The affected area is the front of the torso. Self-categorized by the patient as a rash. Close-up view. The patient did not report lesion symptoms. The contributor reports the lesion is flat. Present for about one day. Female contributor, age 60–69.
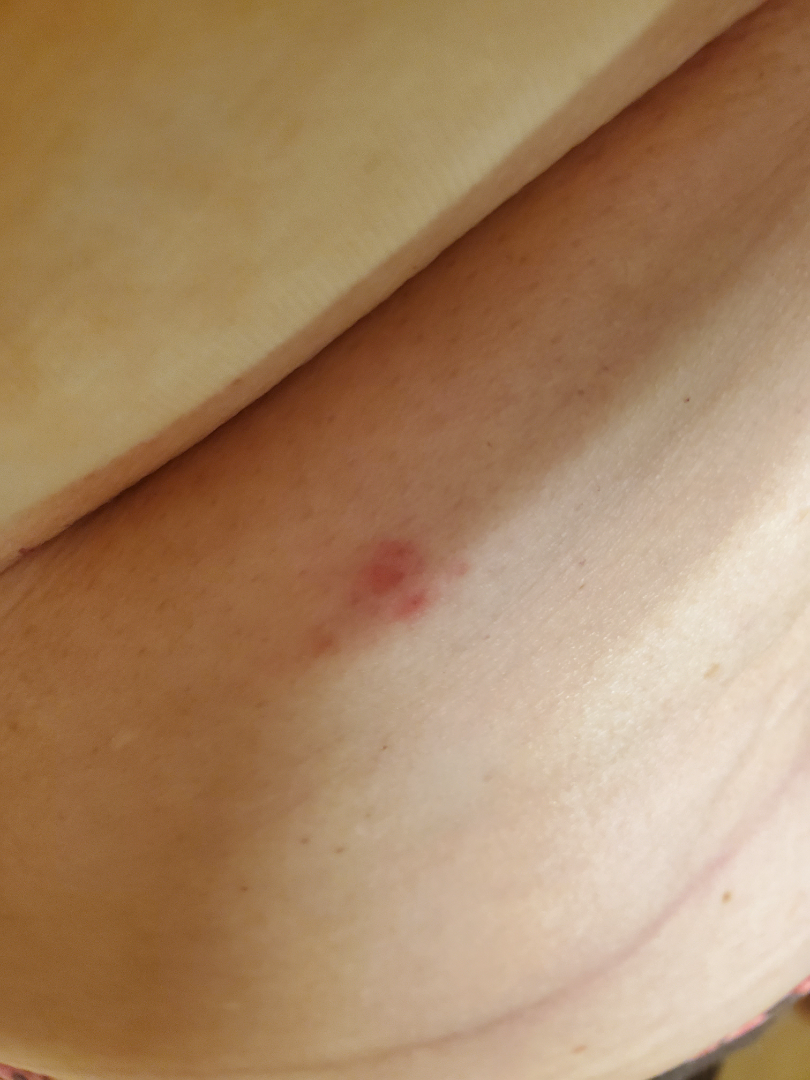The skin condition could not be confidently assessed from this image.